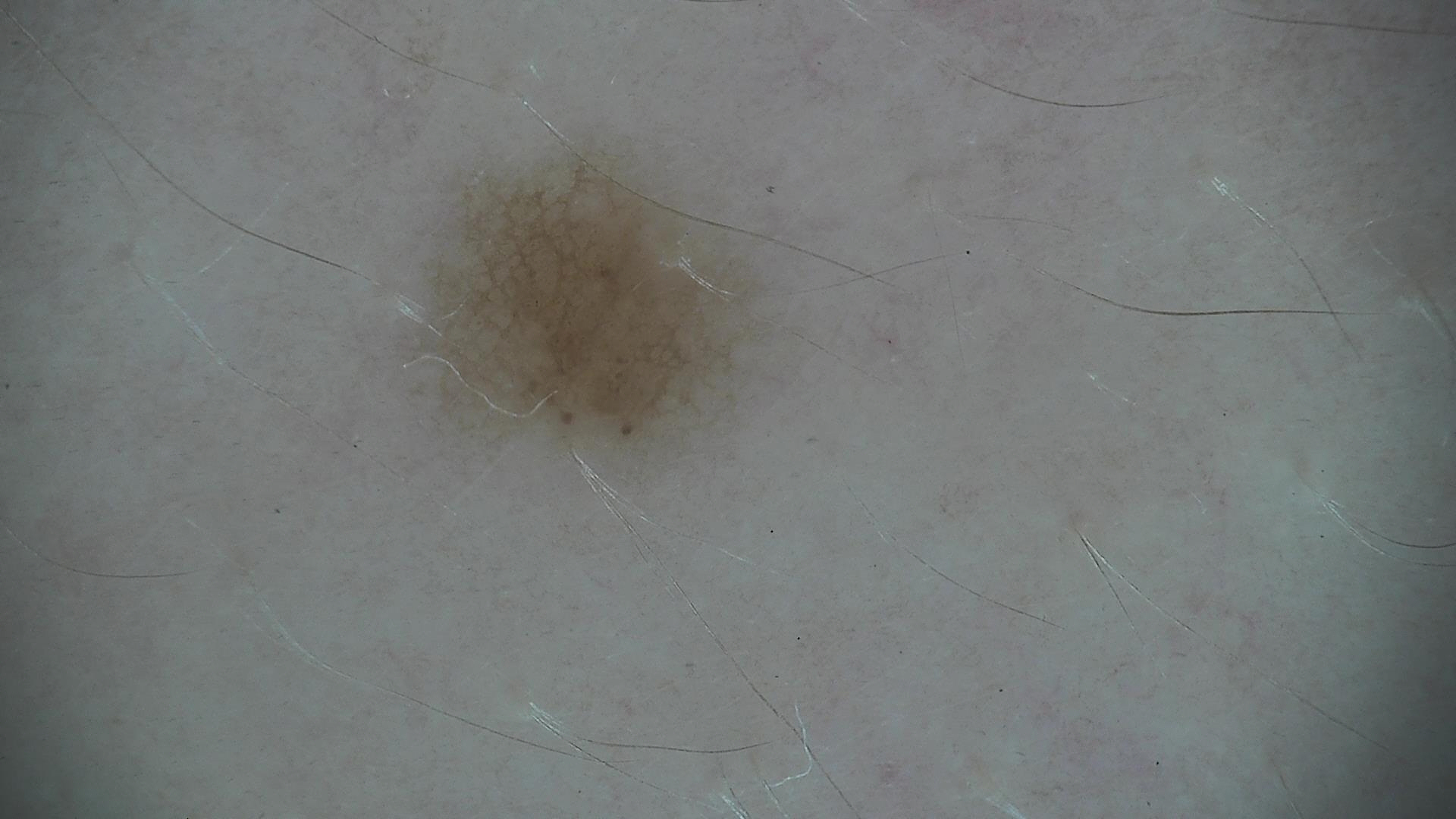Case: A dermoscopic close-up of a skin lesion. Impression: The diagnosis was a dysplastic junctional nevus.